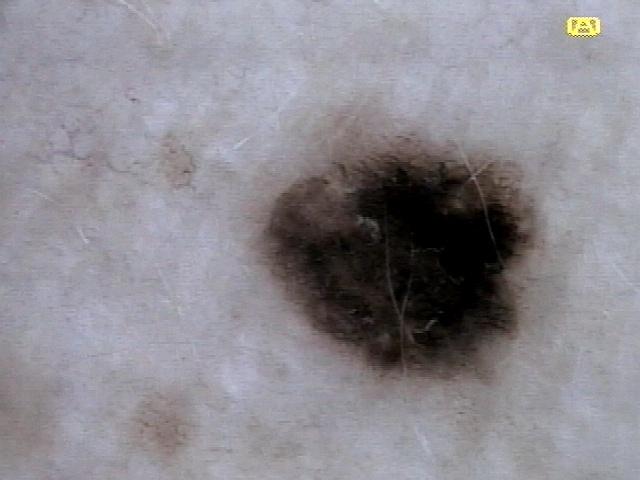{
  "image": "dermatoscopic image",
  "patient": {
    "age_approx": 60,
    "sex": "female"
  },
  "skin_type": "II",
  "lesion_location": {
    "region": "the trunk",
    "detail": "the posterior trunk"
  },
  "diagnosis": {
    "name": "Nevus",
    "malignancy": "benign",
    "confirmation": "histopathology",
    "lineage": "melanocytic"
  }
}